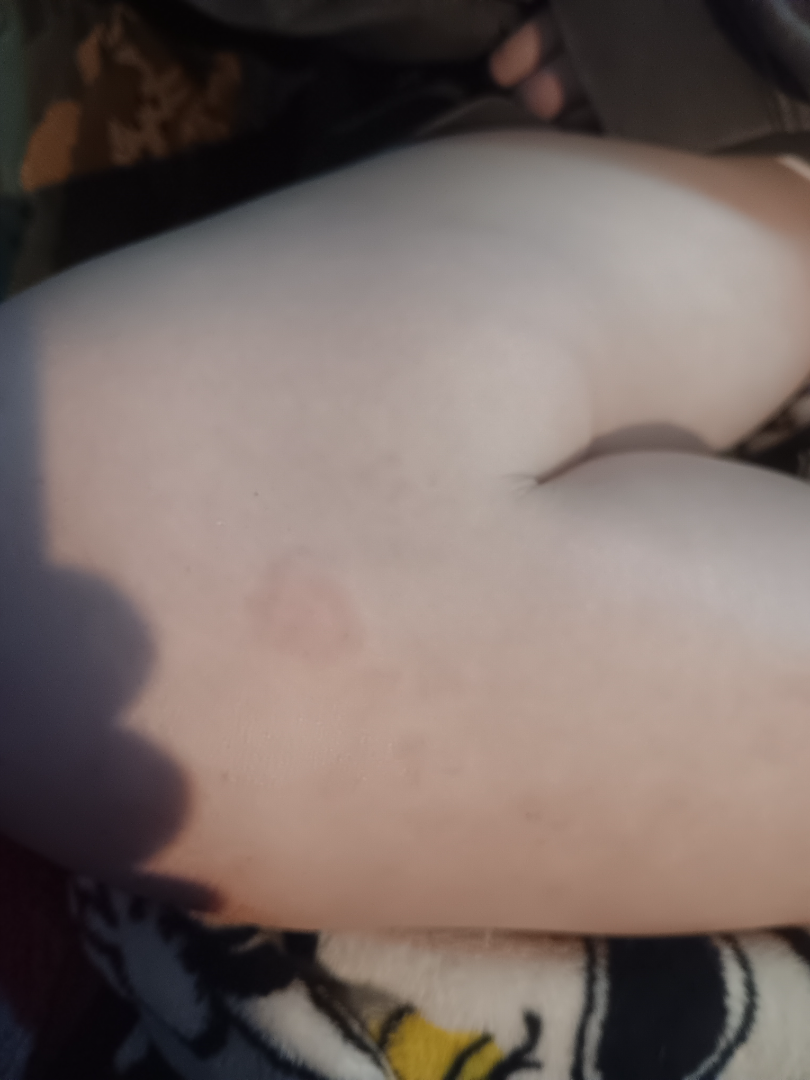The image was not sufficient for the reviewer to characterize the skin condition.
A close-up photograph.
Symptoms reported: itching.
The patient considered this a rash.